A clinical photo of a skin lesion taken with a smartphone. A male subject in their mid-60s. The chart records prior malignancy (patient or family) and pesticide exposure.
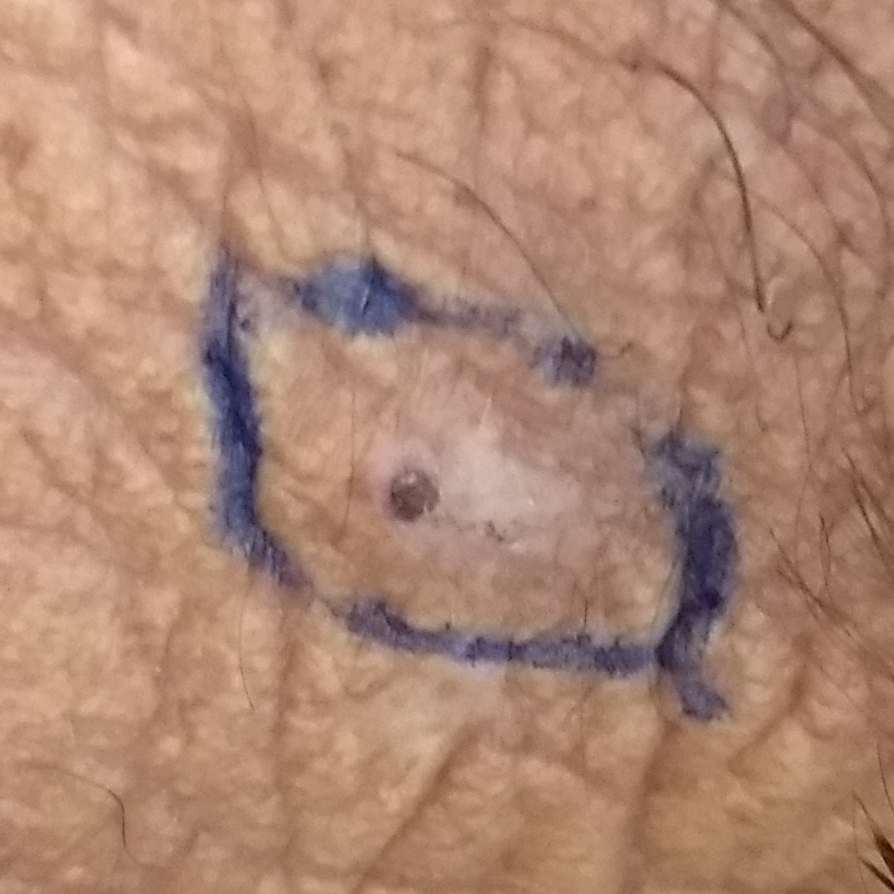{
  "lesion_location": "the neck",
  "lesion_size": {
    "diameter_1_mm": 5.0,
    "diameter_2_mm": 3.0
  },
  "symptoms": {
    "present": [
      "itching"
    ],
    "absent": [
      "pain",
      "bleeding"
    ]
  },
  "diagnosis": {
    "name": "actinic keratosis",
    "code": "ACK",
    "malignancy": "indeterminate",
    "confirmation": "histopathology"
  }
}